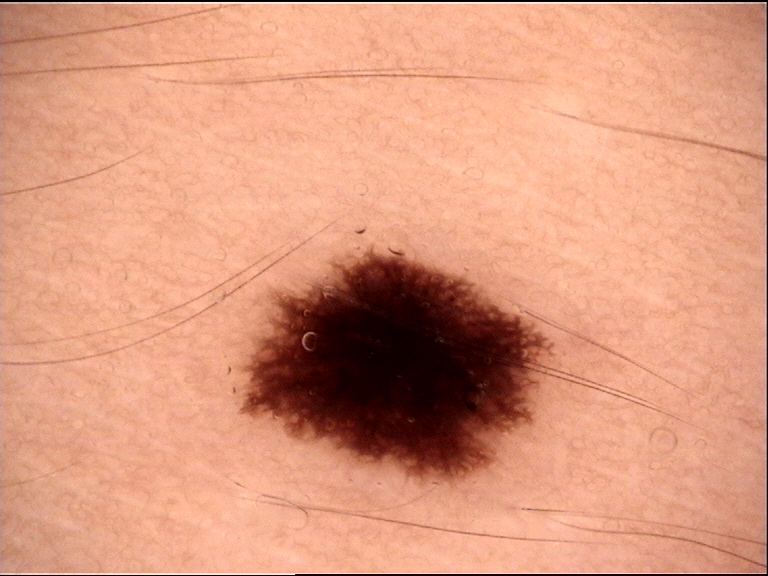modality = dermatoscopy | diagnosis = dysplastic junctional nevus (expert consensus).